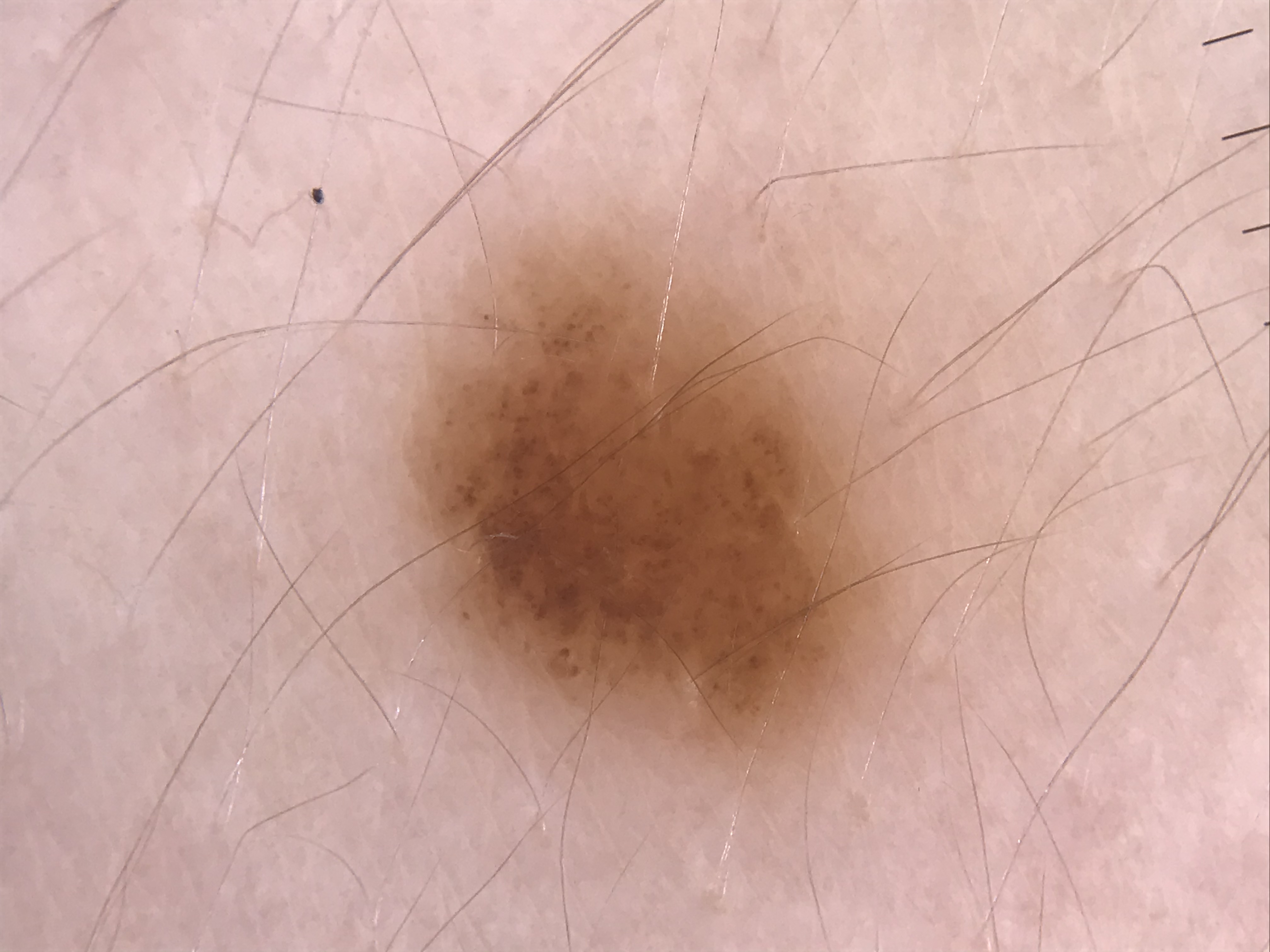{"image": "dermoscopy", "diagnosis": {"name": "dysplastic junctional nevus", "code": "jd", "malignancy": "benign", "super_class": "melanocytic", "confirmation": "expert consensus"}}